The arm is involved; male contributor, age 30–39; the photograph is a close-up of the affected area: 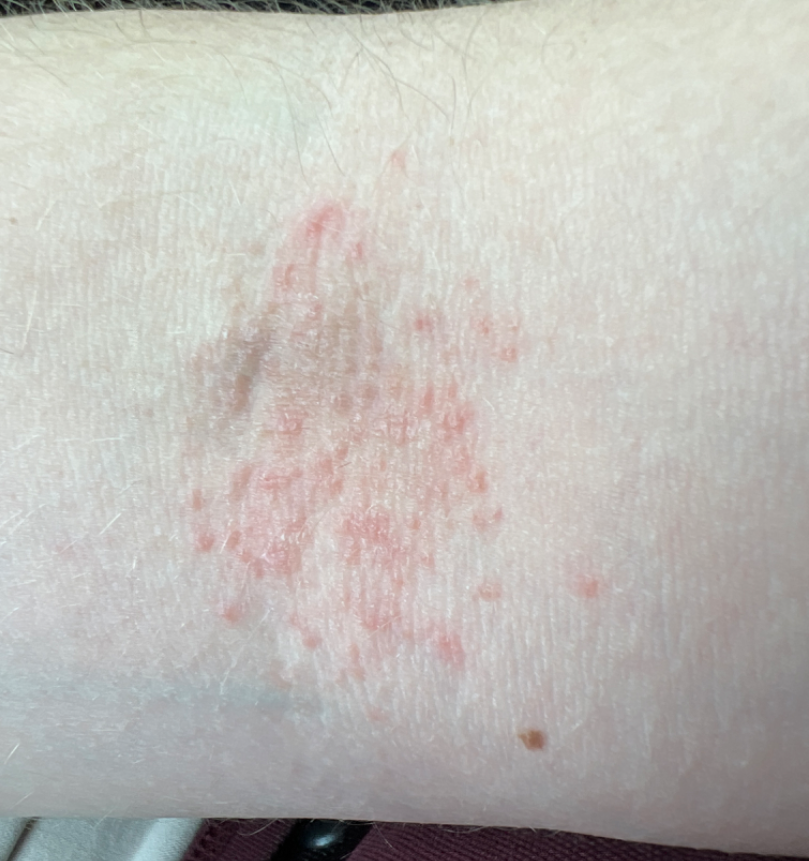Symptoms reported: darkening and itching. Self-categorized by the patient as a rash. The condition has been present for one to four weeks. Skin tone: FST II. No relevant systemic symptoms. Texture is reported as rough or flaky. On remote review of the image: Eczema (weight 0.86); Allergic Contact Dermatitis (weight 0.14).